The photograph was taken at a distance; skin tone: Fitzpatrick II; the patient reports the lesion is raised or bumpy; the leg is involved; present for one to four weeks.
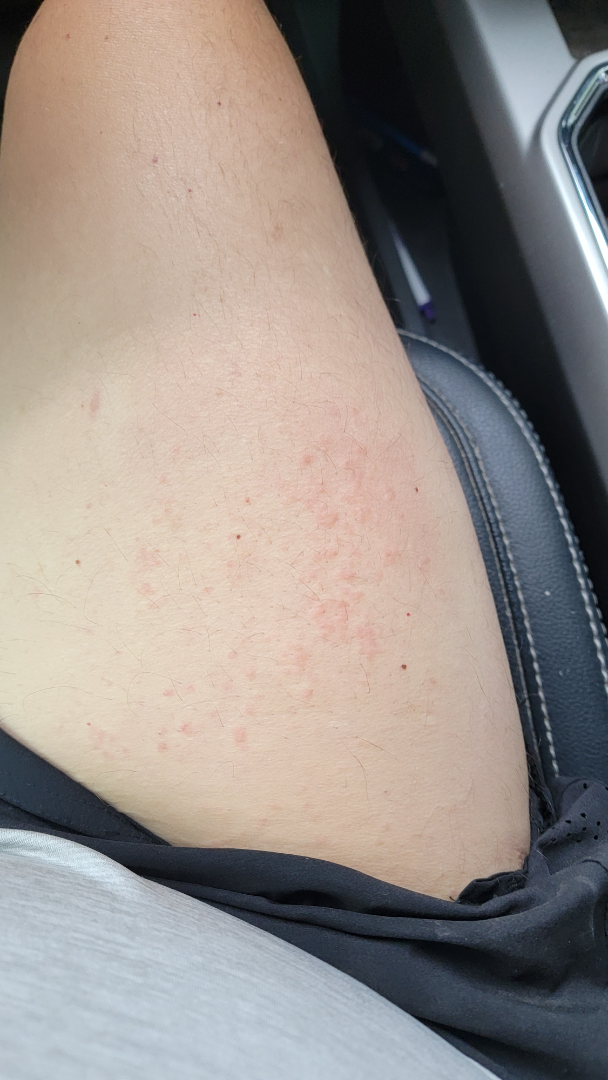{"differential": {"Urticaria": 0.33, "Eczema": 0.33, "Allergic Contact Dermatitis": 0.33}}